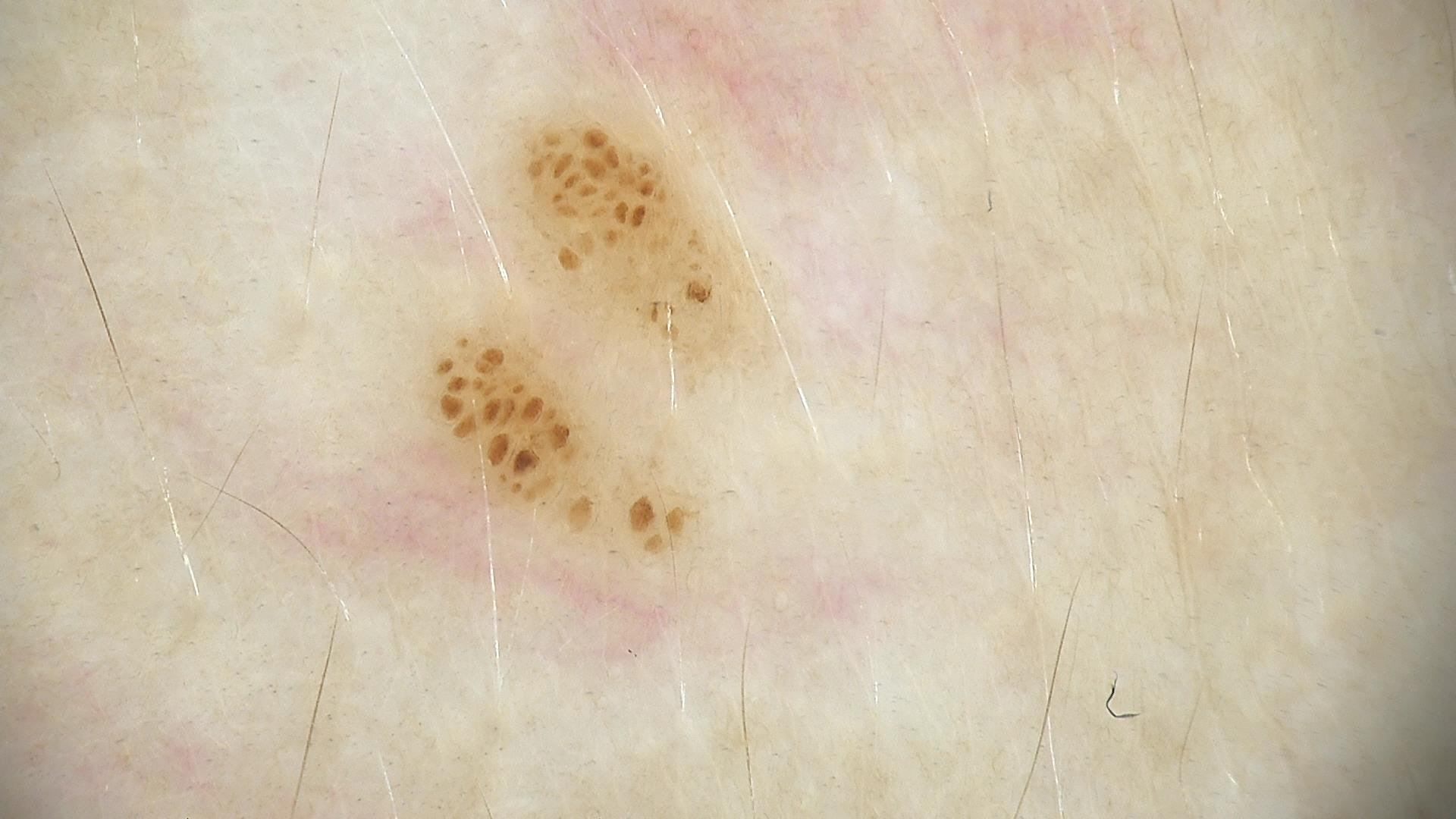Impression: Labeled as a dysplastic junctional nevus.